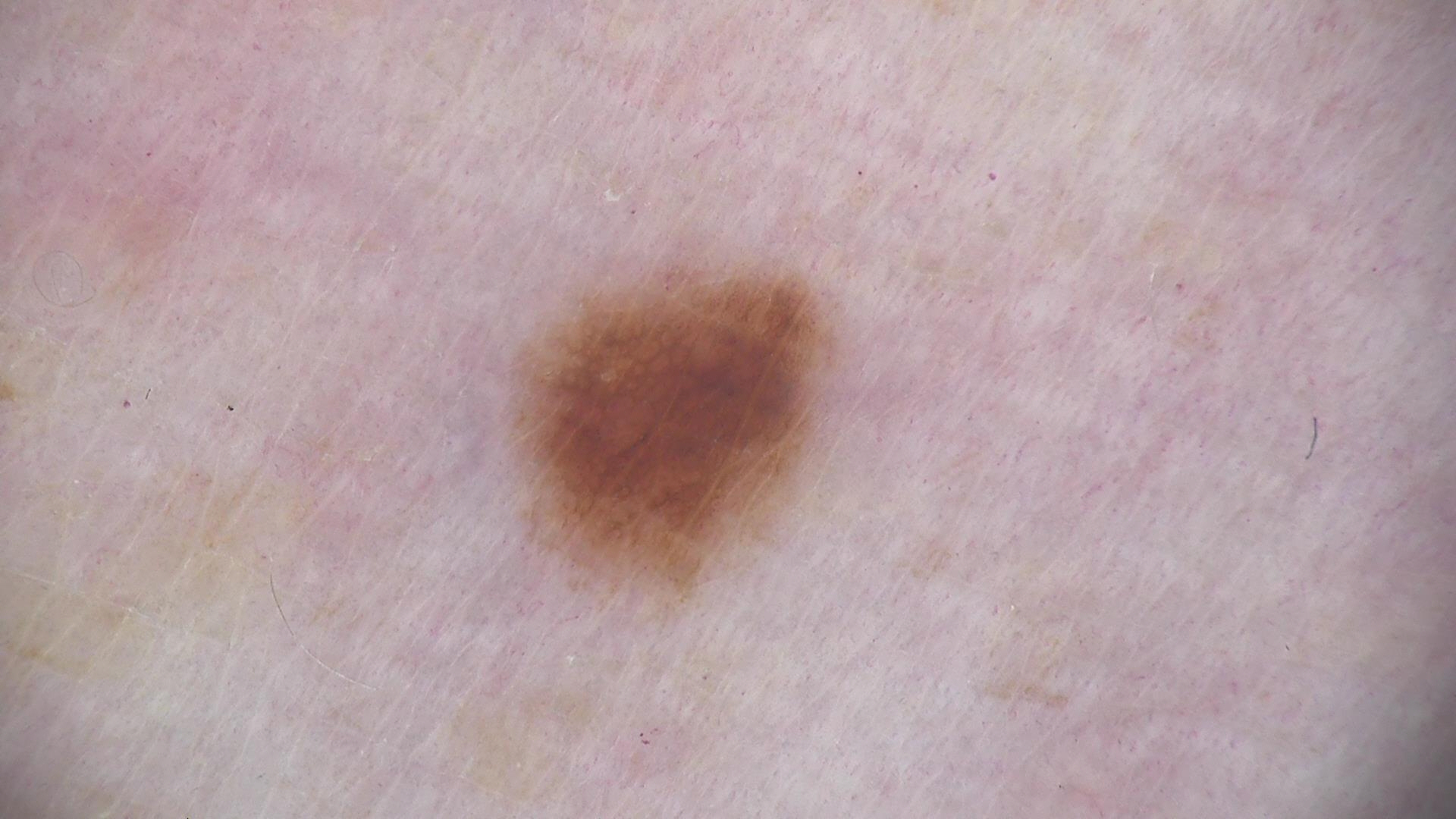The diagnosis was a dysplastic junctional nevus.